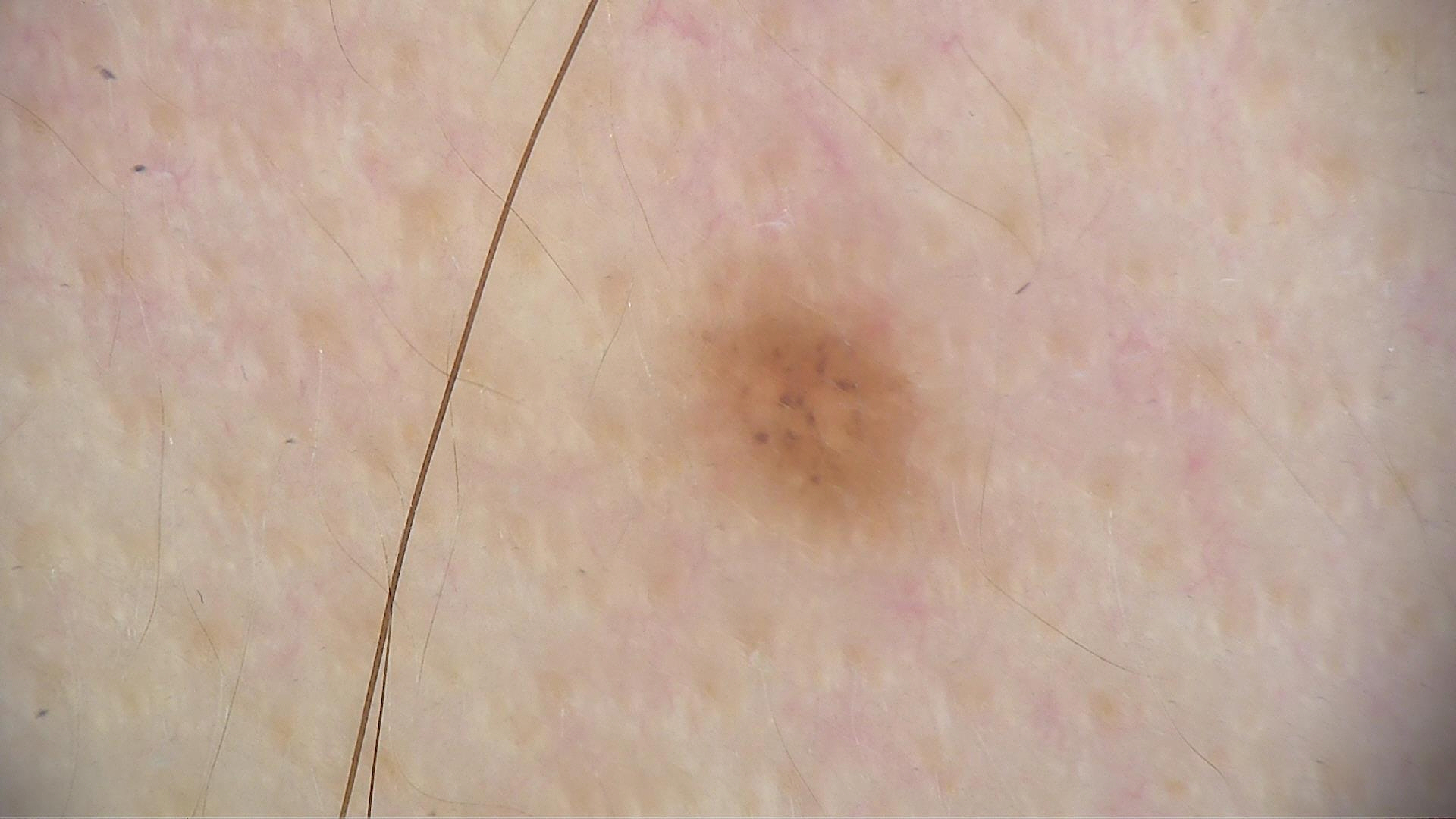{
  "diagnosis": {
    "name": "dysplastic junctional nevus",
    "code": "jd",
    "malignancy": "benign",
    "super_class": "melanocytic",
    "confirmation": "expert consensus"
  }
}